This image was taken at an angle.
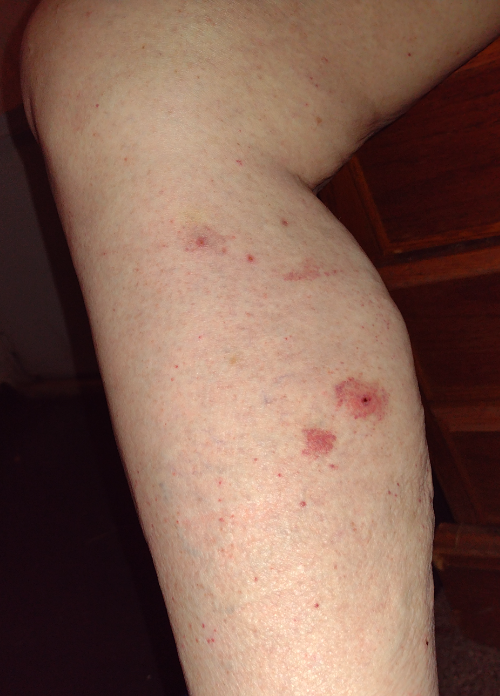  differential:
    leading:
      - Pigmented purpuric eruption
    considered:
      - Purpura